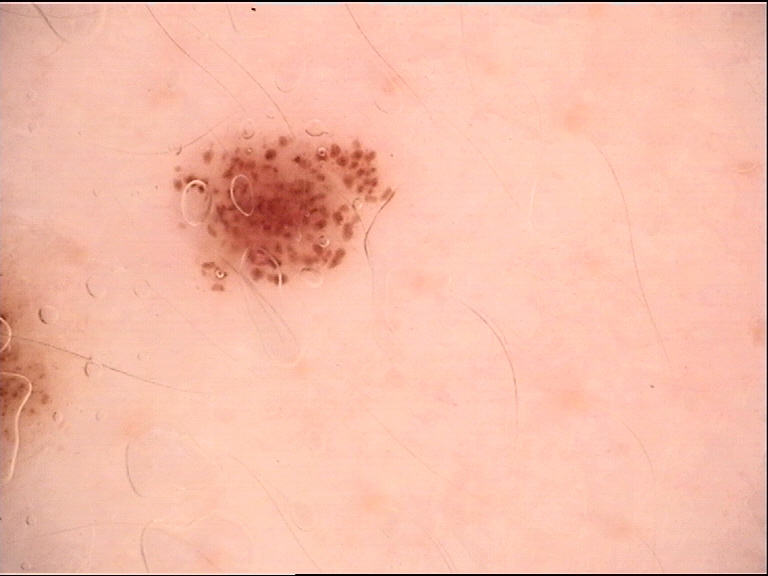image=dermatoscopy
assessment=dysplastic junctional nevus (expert consensus)